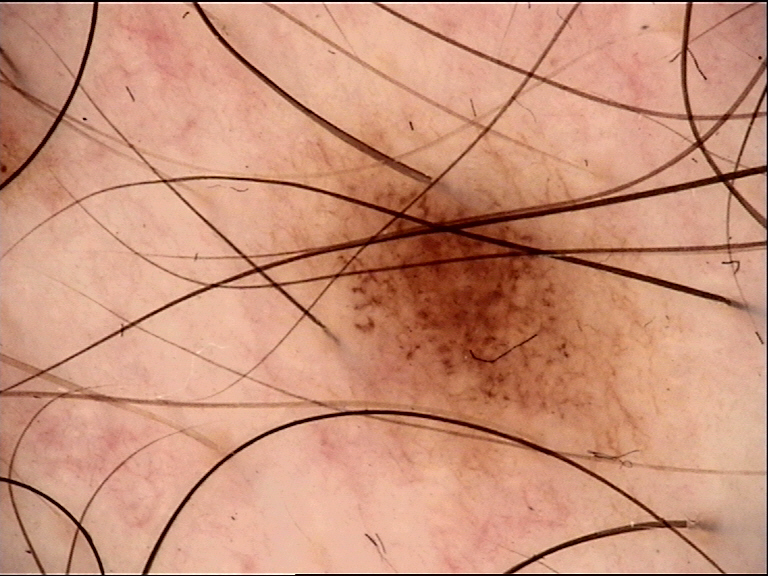Consistent with a dysplastic junctional nevus.